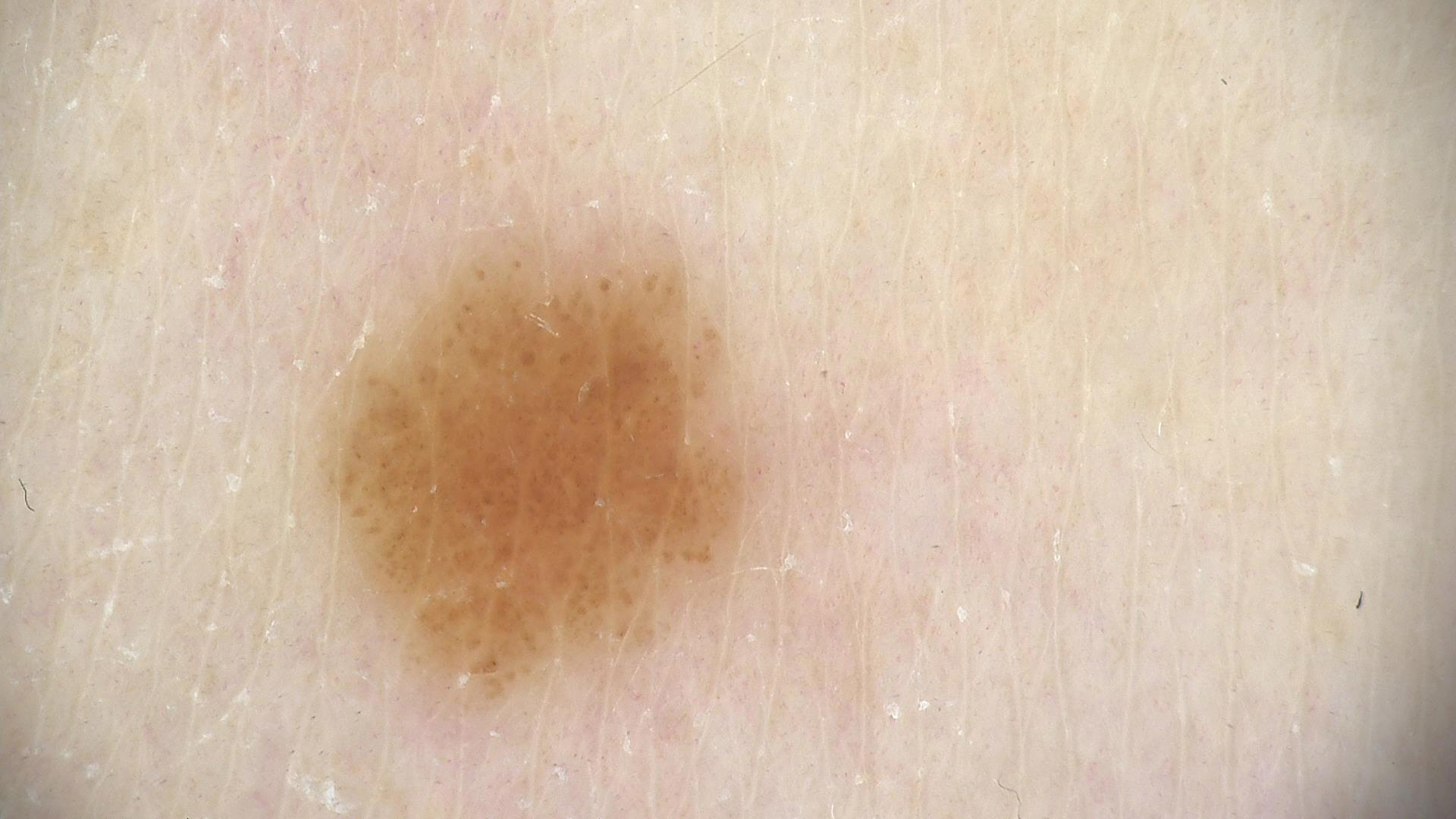imaging = dermoscopy; lesion type = banal; class = compound nevus (expert consensus).